A dermoscopic close-up of a skin lesion · the patient is a male aged around 65:
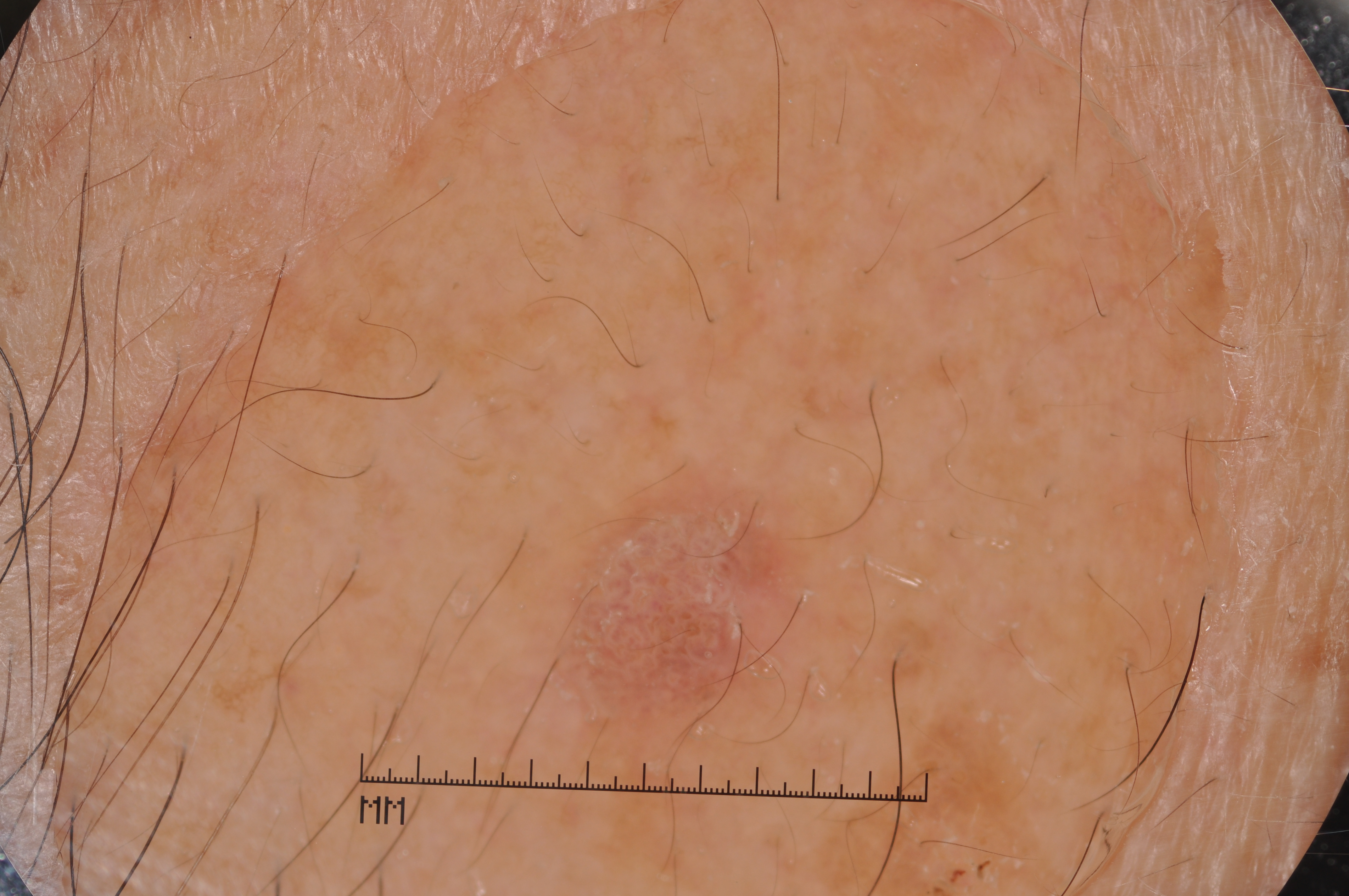Q: What does dermoscopy show?
A: milia-like cysts
Q: Where is the lesion in the image?
A: bbox(542, 457, 823, 765)
Q: What did the assessment conclude?
A: a seborrheic keratosis